A dermatoscopic image of a skin lesion.
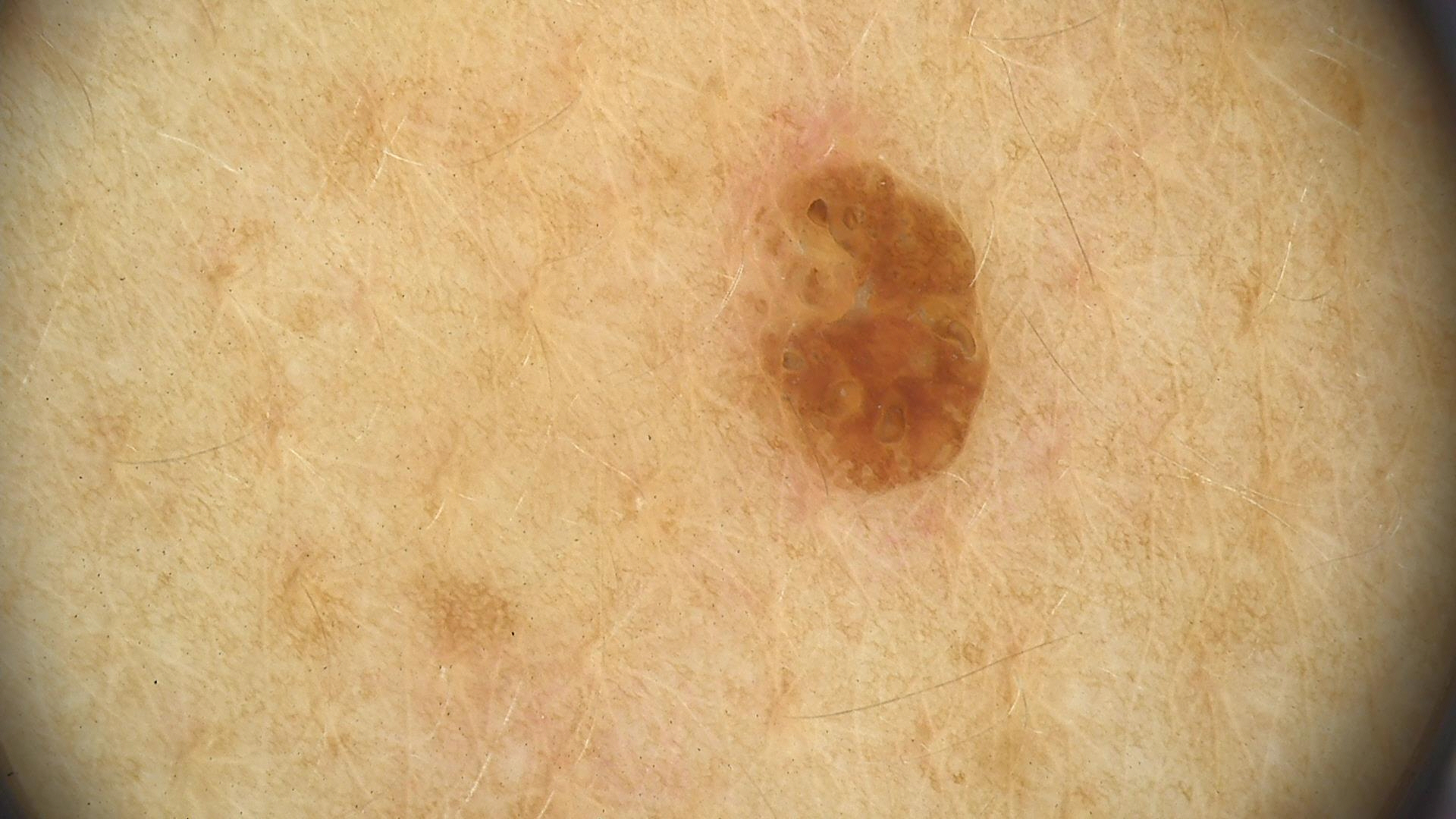The architecture is that of a keratinocytic lesion. The diagnosis was a seborrheic keratosis.